A dermoscopy image of a single skin lesion.
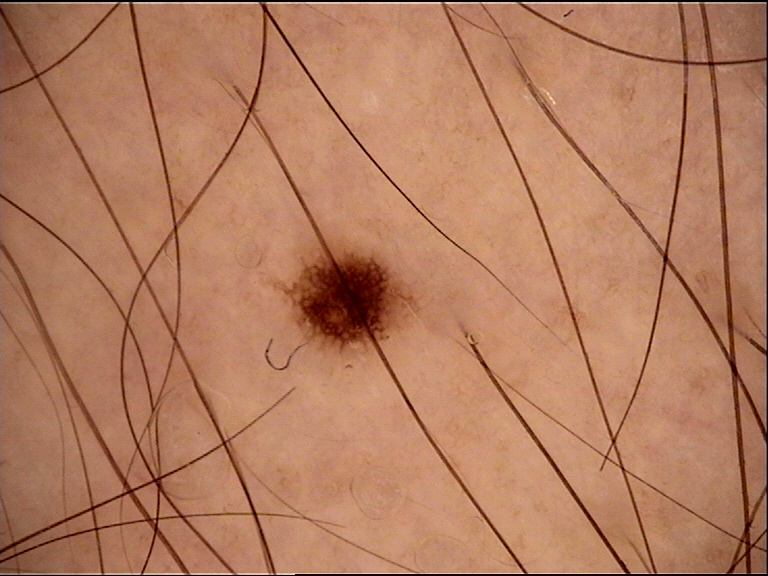Conclusion:
The diagnostic label was a benign lesion — a dysplastic junctional nevus.